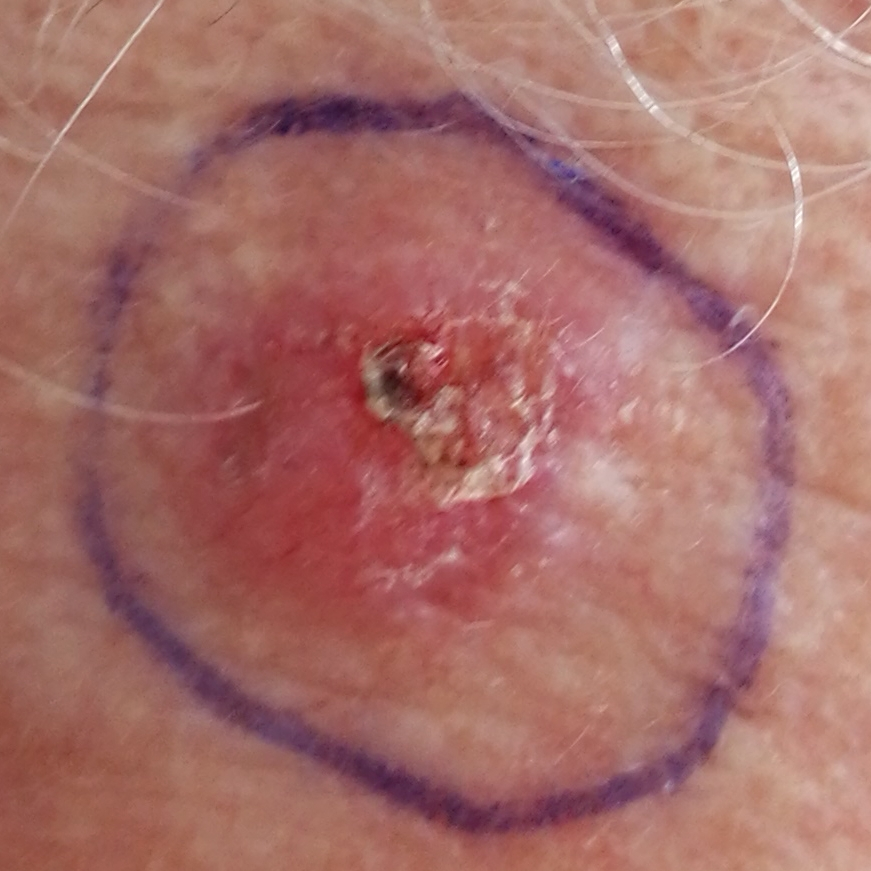Histopathological examination showed a basal cell carcinoma.